A skin lesion imaged with a dermatoscope.
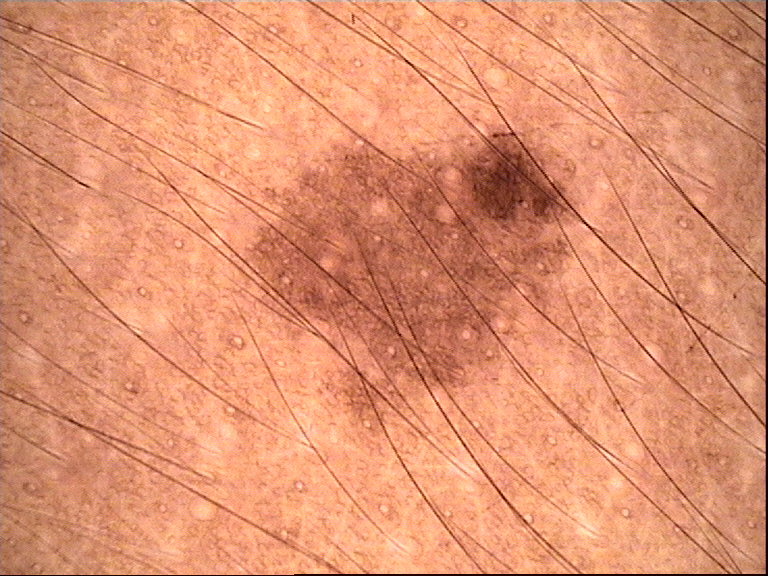Consistent with a dysplastic junctional nevus.